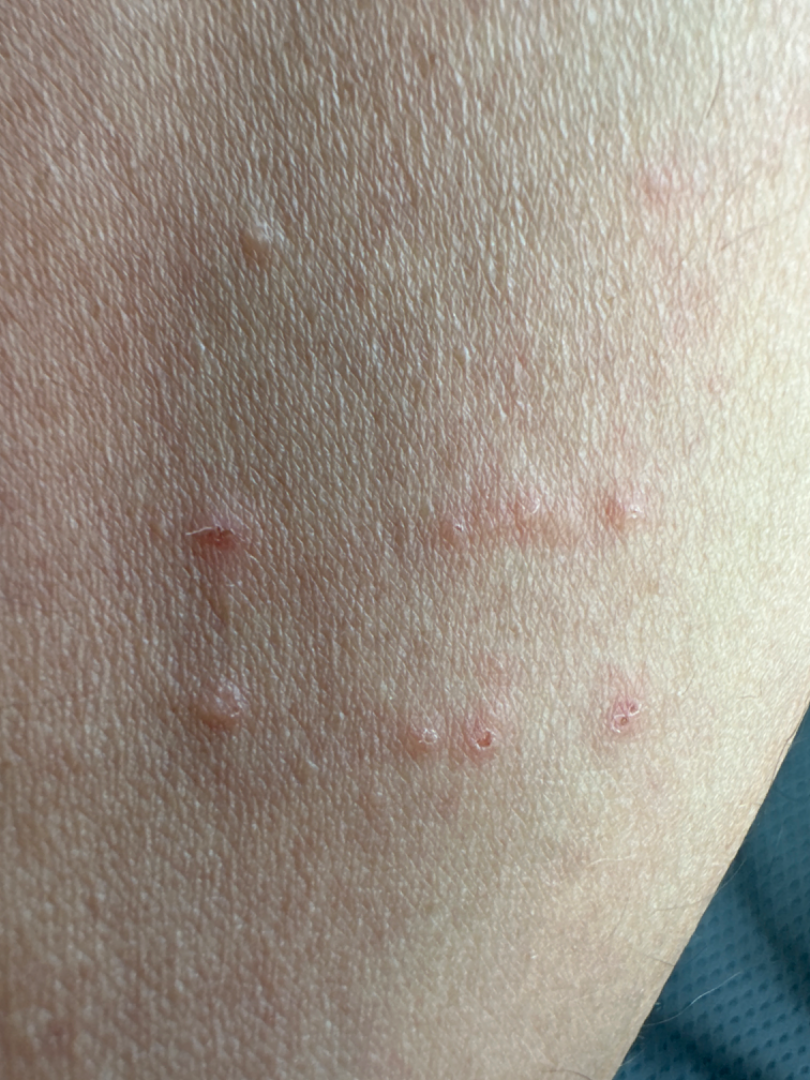| field | value |
|---|---|
| diagnostic considerations | the leading impression is Molluscum Contagiosum; possibly Insect Bite; also consider Allergic Contact Dermatitis |